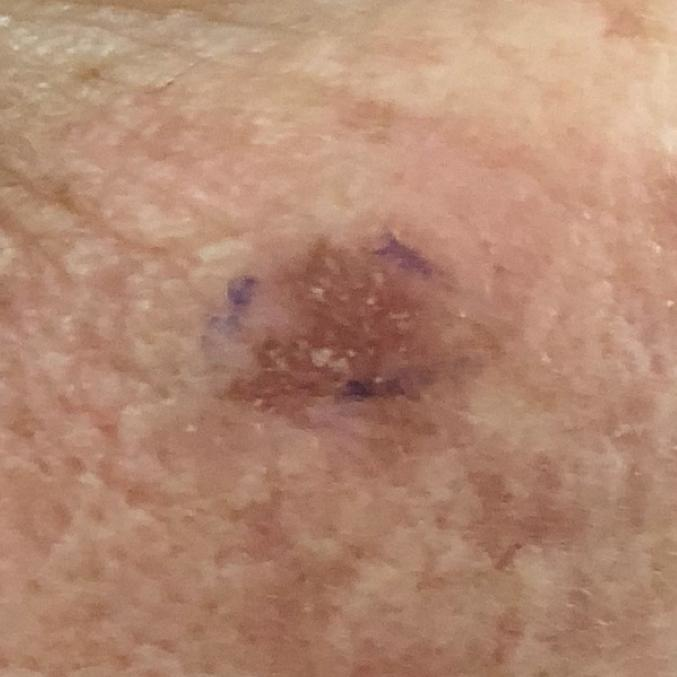{
  "patient": {
    "age": 60
  },
  "image": "clinical photo",
  "lesion_location": "the face",
  "symptoms": {
    "present": [
      "itching"
    ]
  },
  "diagnosis": {
    "name": "actinic keratosis",
    "code": "ACK",
    "malignancy": "indeterminate",
    "confirmation": "clinical consensus"
  }
}